This is a close-up image · female contributor, age 50–59 · Fitzpatrick phototype III; non-clinician graders estimated 2 on the MST · self-categorized by the patient as a rash:
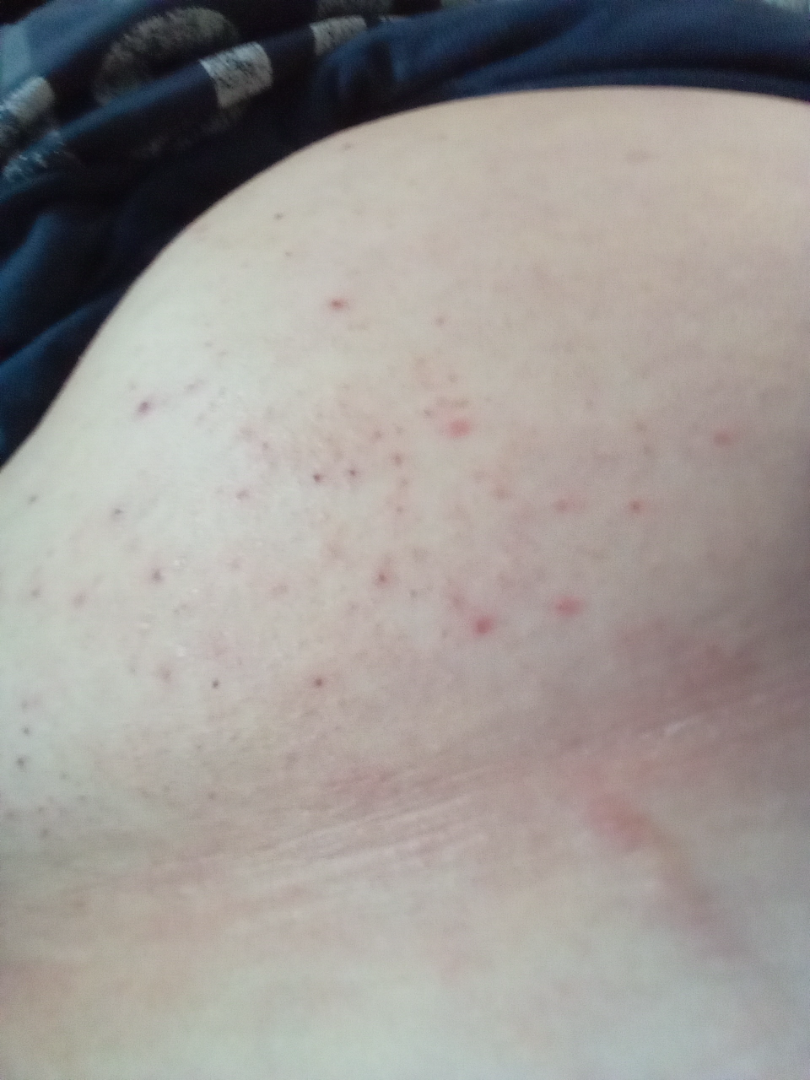differential = Folliculitis (100%).